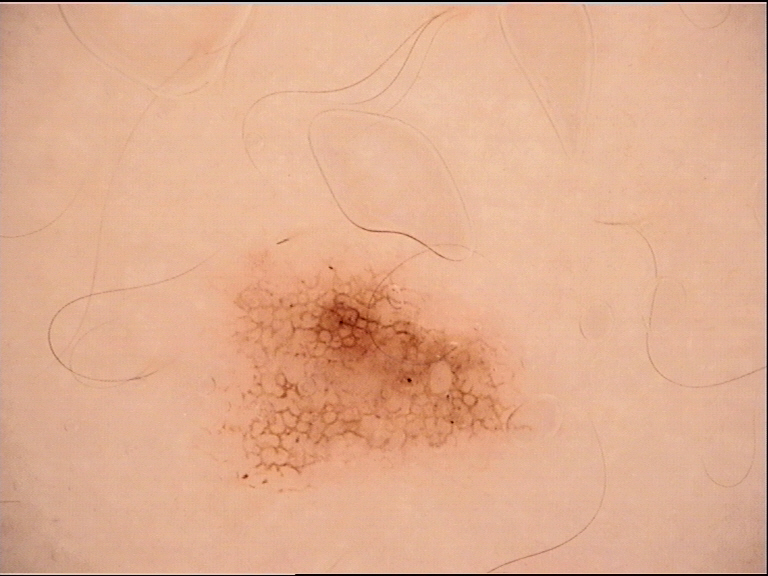Summary: A dermoscopy image of a single skin lesion. Conclusion: Consistent with a benign lesion — a dysplastic junctional nevus.